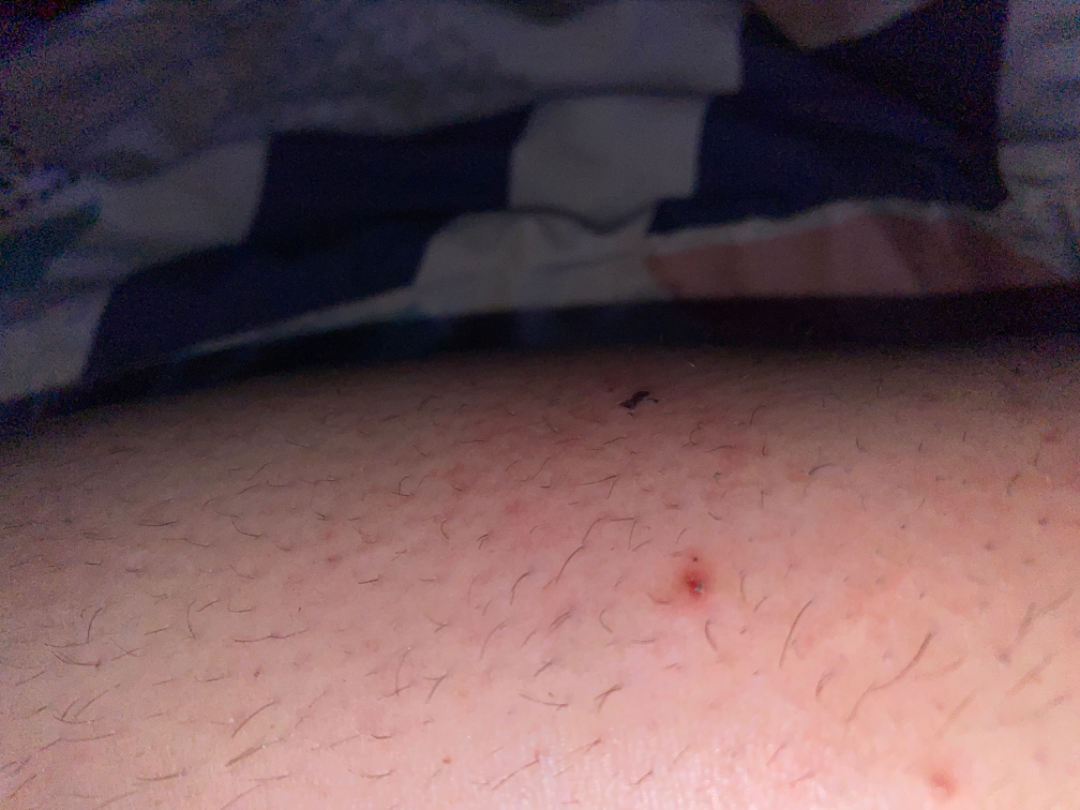Case summary:
* impression · Folliculitis (26%); Acute dermatitis, NOS (15%); Ingrown hair (12%); Insect Bite (12%); Infection of tick bite (12%); Eczema (12%); Hypersensitivity (12%)